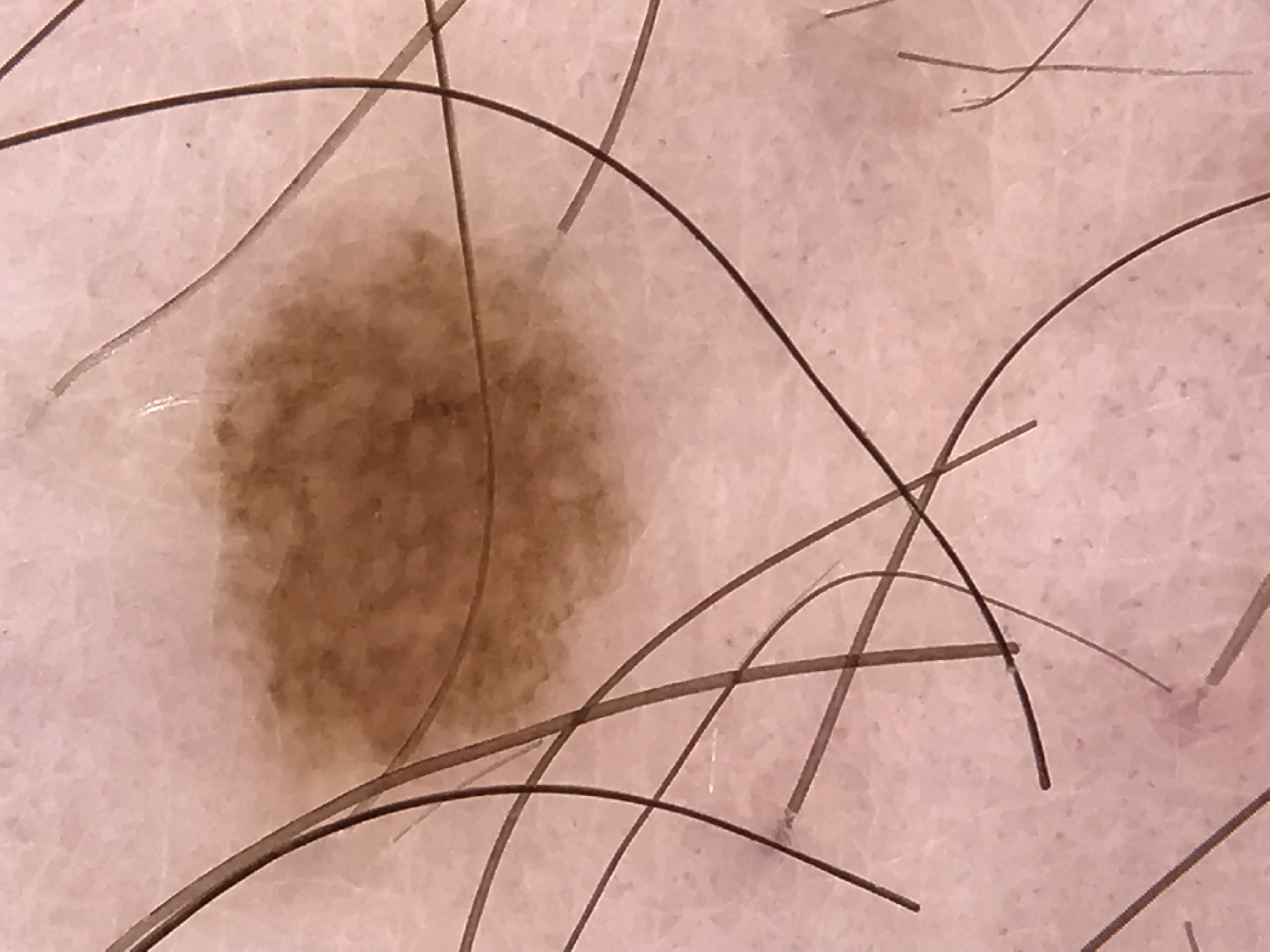label=junctional nevus (expert consensus)